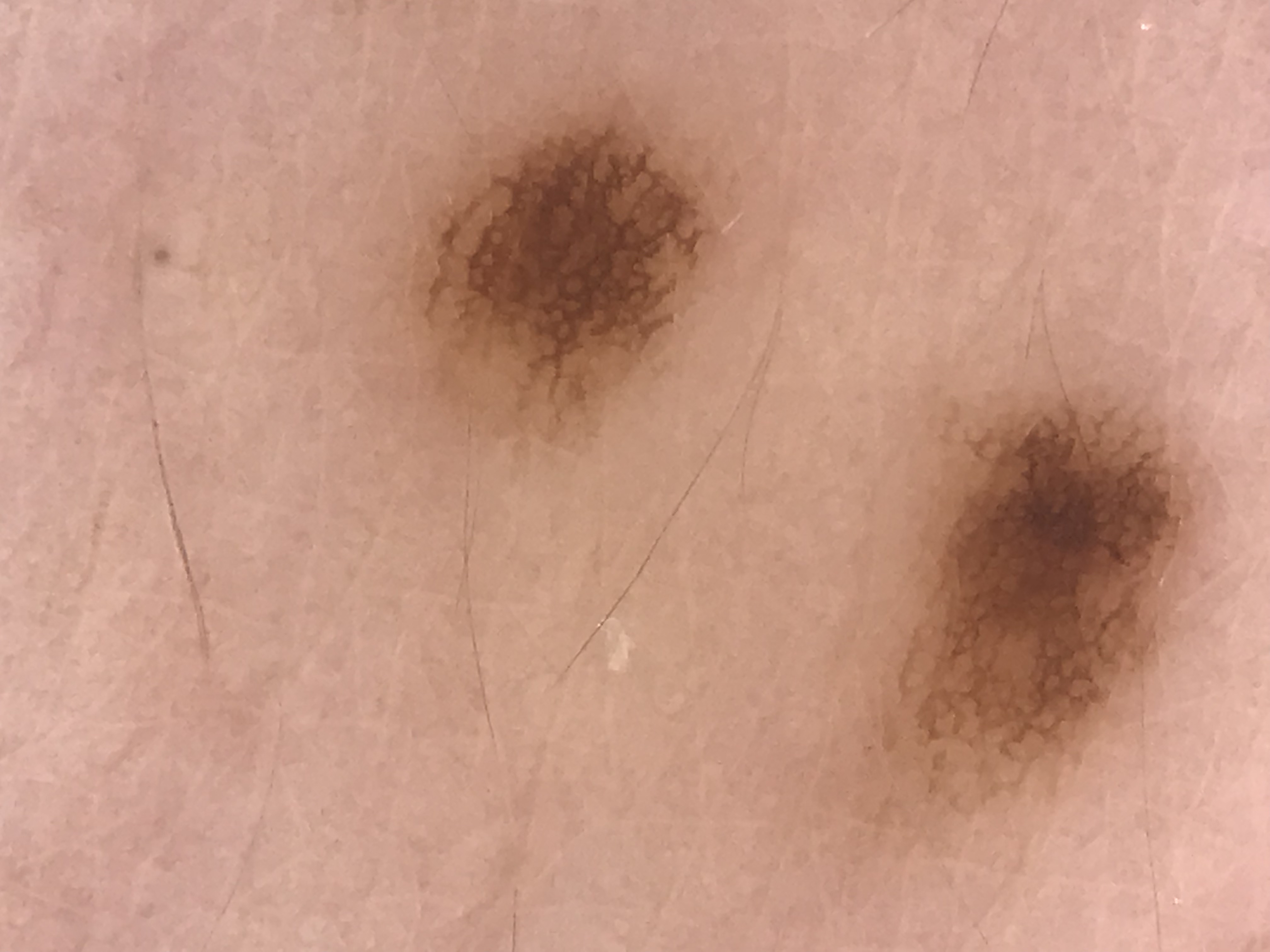A dermoscopic photograph of a skin lesion. This is a banal lesion. Classified as a junctional nevus.